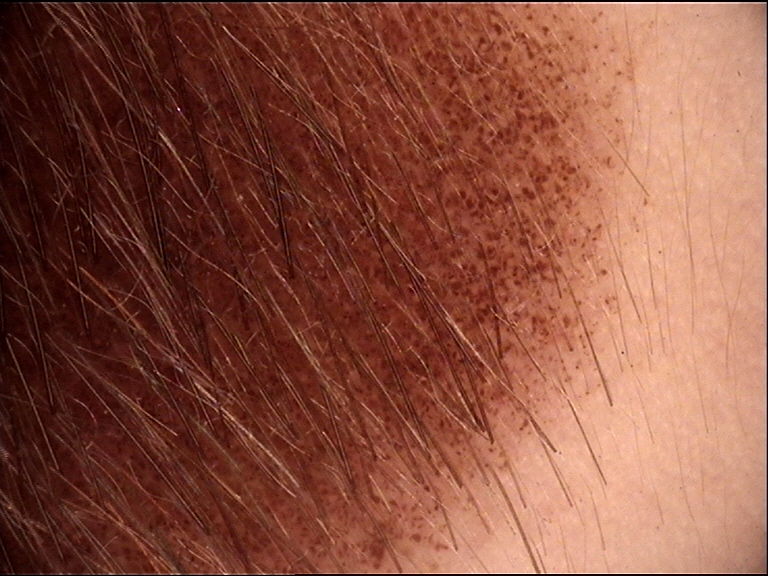class: congenital junctional nevus (expert consensus).